The photograph was taken at an angle; the lesion involves the leg; the patient reports bothersome appearance; the condition has been present for less than one week; the lesion is described as raised or bumpy: 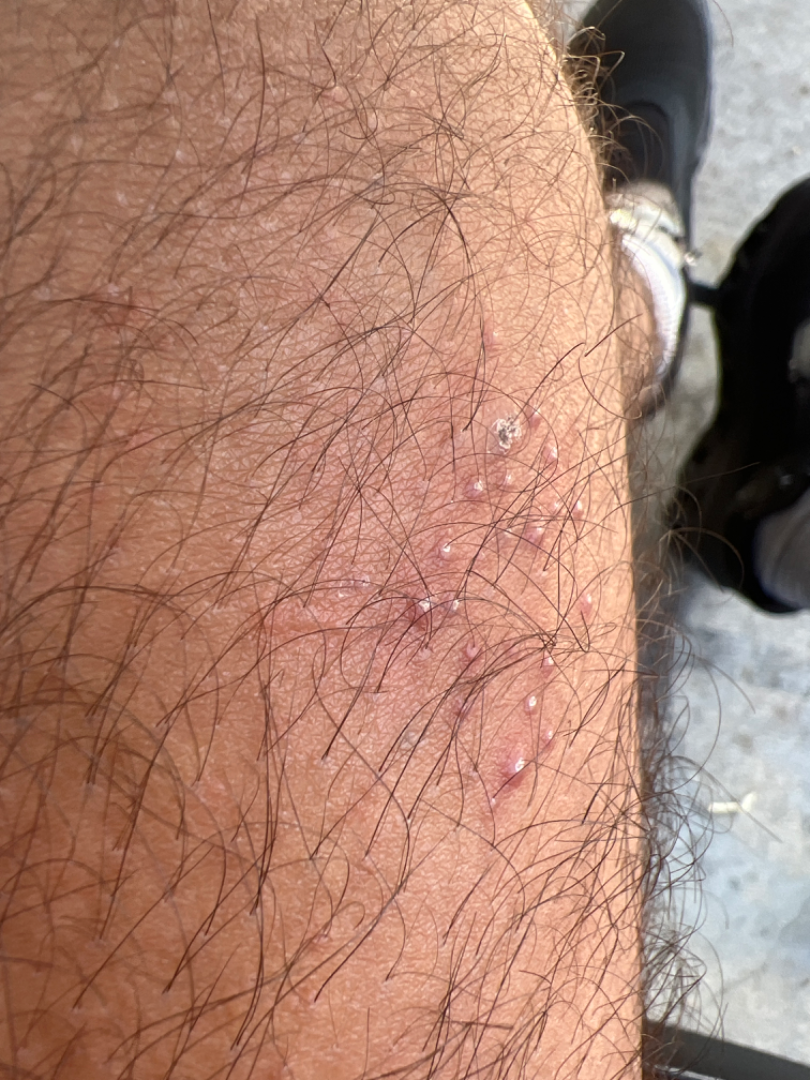Assessment:
The reviewing dermatologist's impression was: most likely Herpes Simplex; also raised was Folliculitis.